A dermoscopic photograph of a skin lesion.
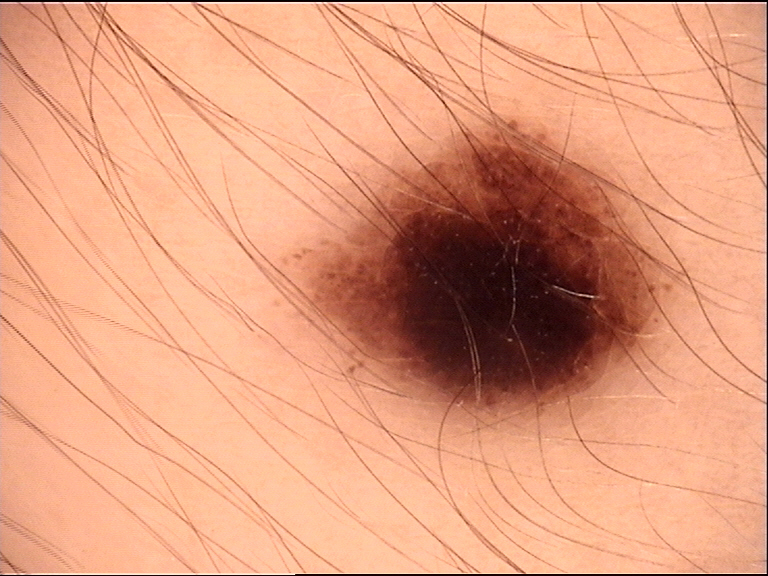Diagnosed as a banal lesion — a junctional nevus.